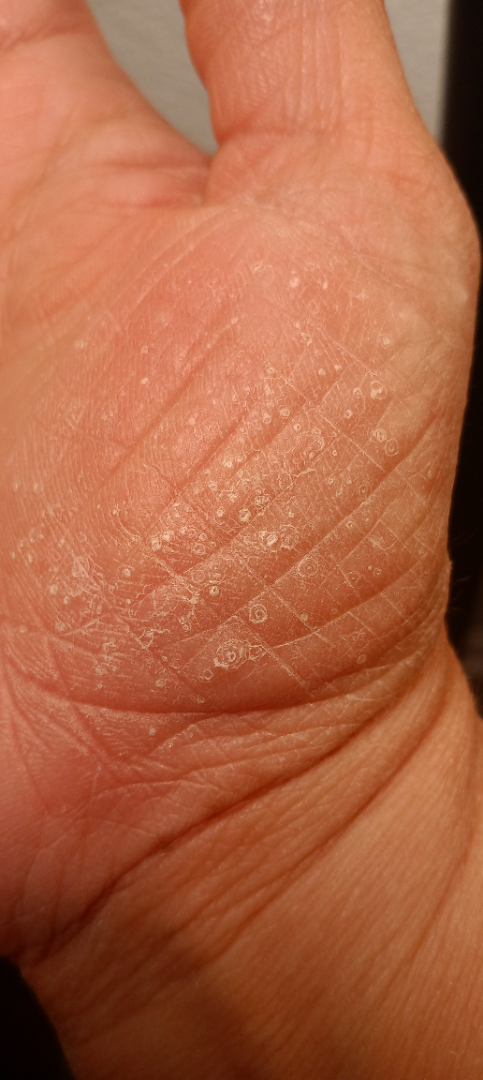Patient information: The patient notes associated mouth sores. The patient considered this a rash. Female subject, age 40–49. Texture is reported as rough or flaky and raised or bumpy. The affected area is the palm. The lesion is associated with pain, bothersome appearance, enlargement and itching. A close-up photograph. Review: On remote dermatologist review: Eczema and Psoriasis were considered with similar weight.